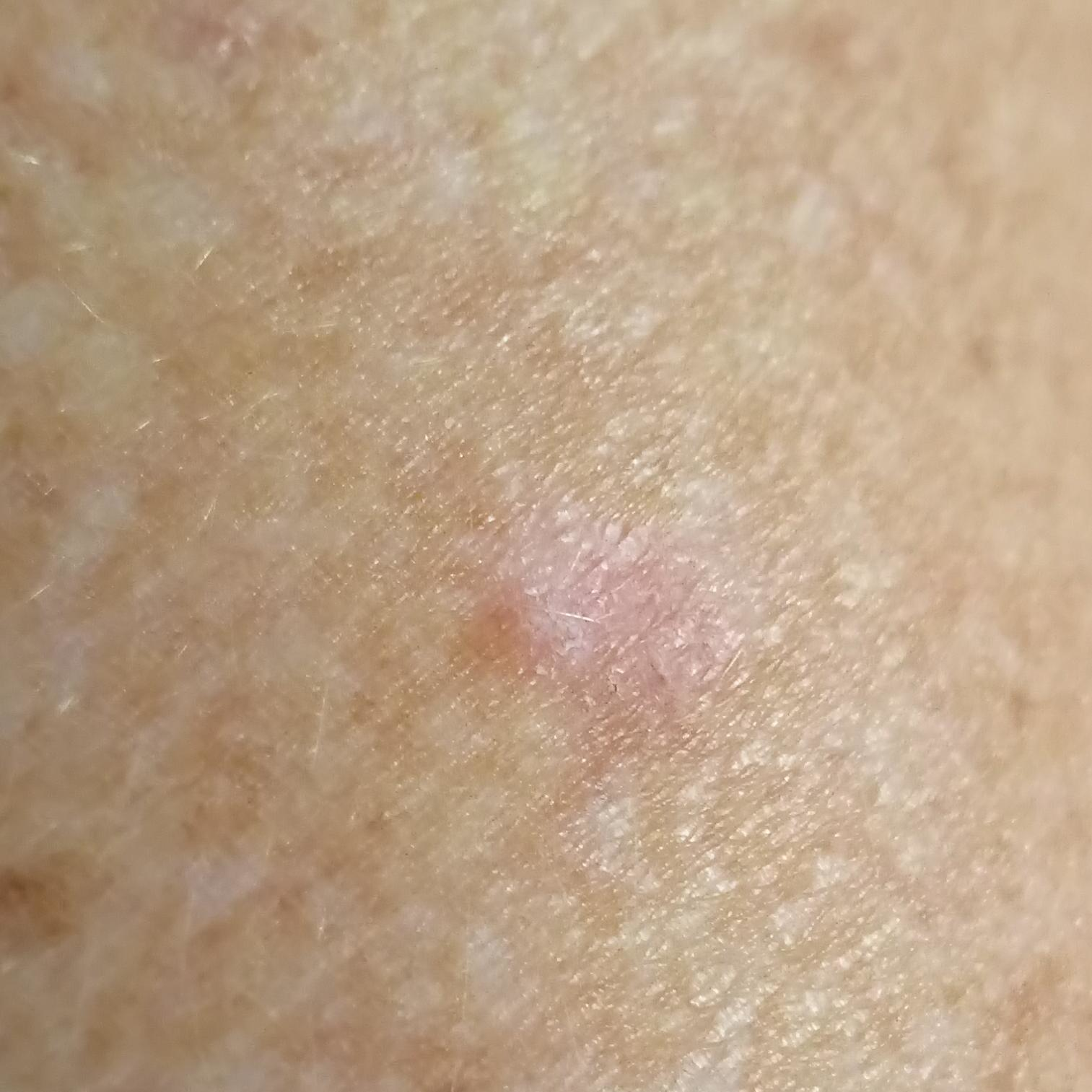Notes:
– modality: clinical photo
– subject: female, in their late 50s
– region: a forearm
– patient-reported symptoms: none reported
– assessment: actinic keratosis (clinical consensus)